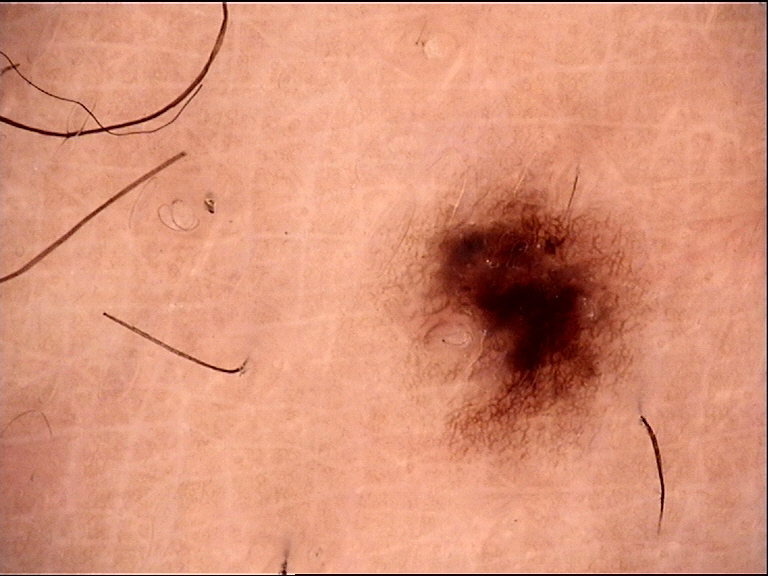Q: What is the imaging modality?
A: dermoscopy
Q: What was the diagnostic impression?
A: dysplastic junctional nevus (expert consensus)